A contact-polarized dermoscopy image of a skin lesion · a female subject aged around 30: 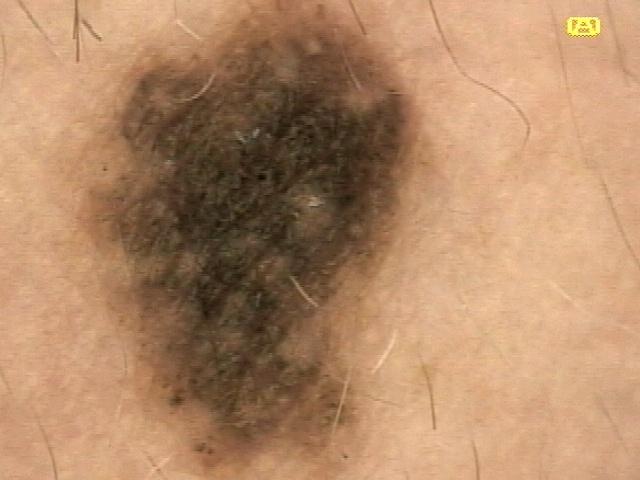Case summary:
The lesion is on the anterior trunk.
Impression:
Expert review favored a nevus.